The patient did not report lesion symptoms; an image taken at an angle; the affected area is the arm; female contributor, age 40–49; reported duration is more than one year:
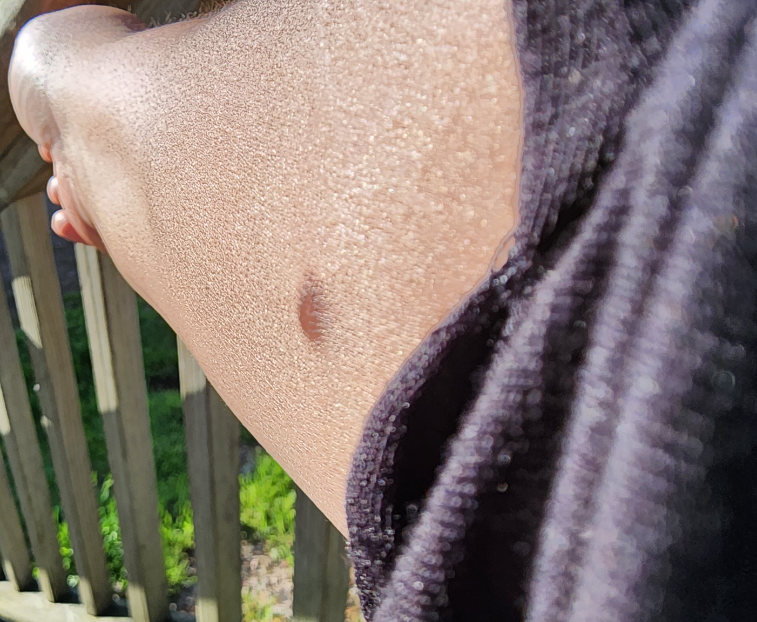<case>
<differential>
  <tied_lead>Dermatofibroma, Neoplasm of uncertain behavior of skin of arm</tied_lead>
  <considered>Pseudolymphoma</considered>
</differential>
</case>